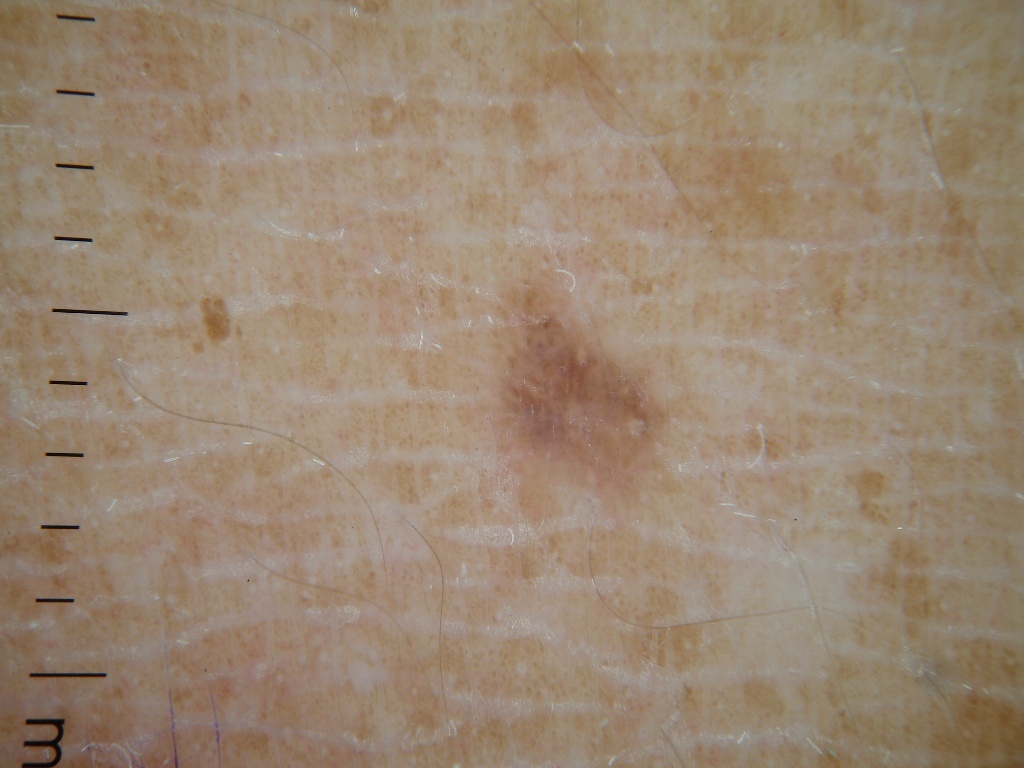patient=female, approximately 30 years of age; imaging=dermoscopic image; absent dermoscopic features=negative network, milia-like cysts, globules, streaks, and pigment network; lesion bbox=<bbox>480, 250, 681, 531</bbox>; diagnosis=a melanocytic nevus.